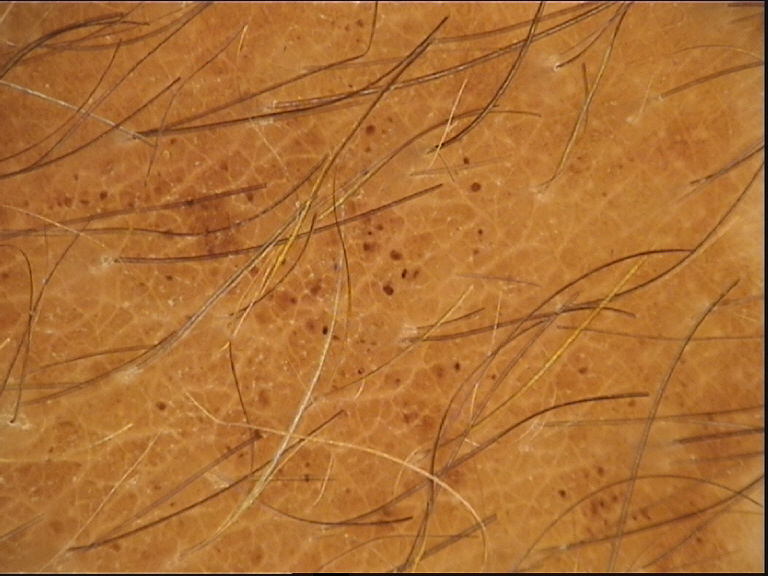The diagnosis was a banal lesion — a congenital compound nevus.